A skin lesion imaged with a dermatoscope.
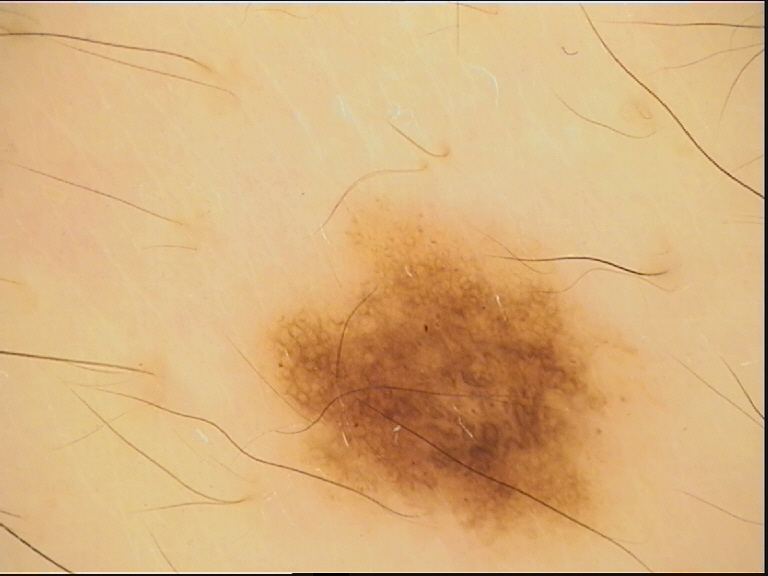diagnosis: dysplastic junctional nevus (expert consensus).